The subject is male, the photograph was taken at an angle, the lesion involves the arm and front of the torso: 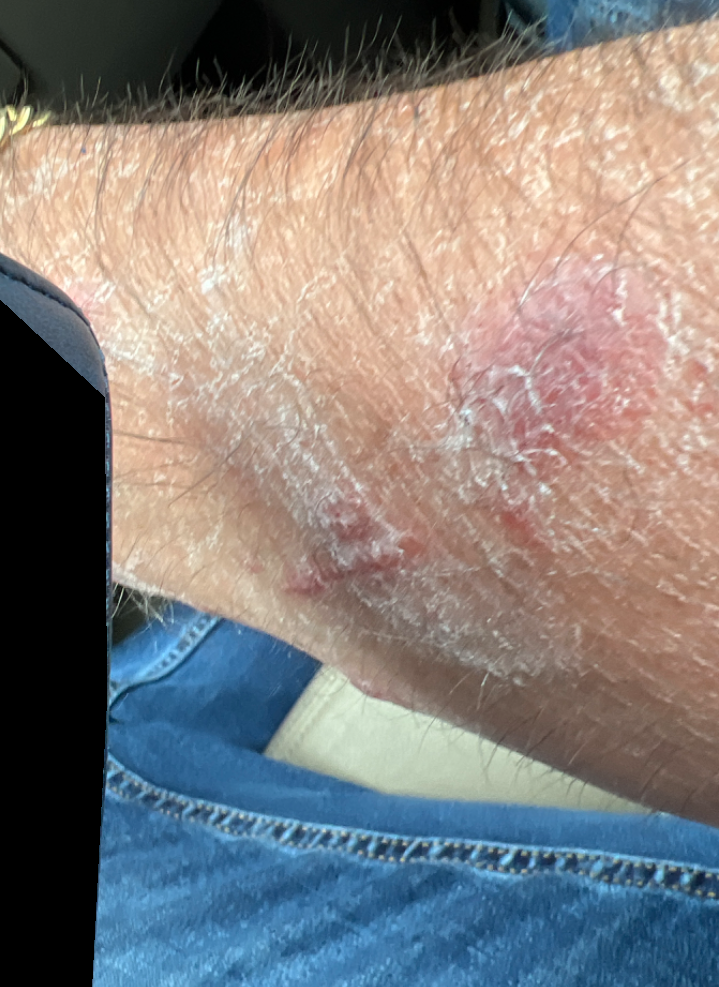The condition has been present for less than one week. The patient considered this a rash. No associated systemic symptoms reported. Reported lesion symptoms include itching. Texture is reported as fluid-filled. The impression was split between Allergic Contact Dermatitis and Contact dermatitis.